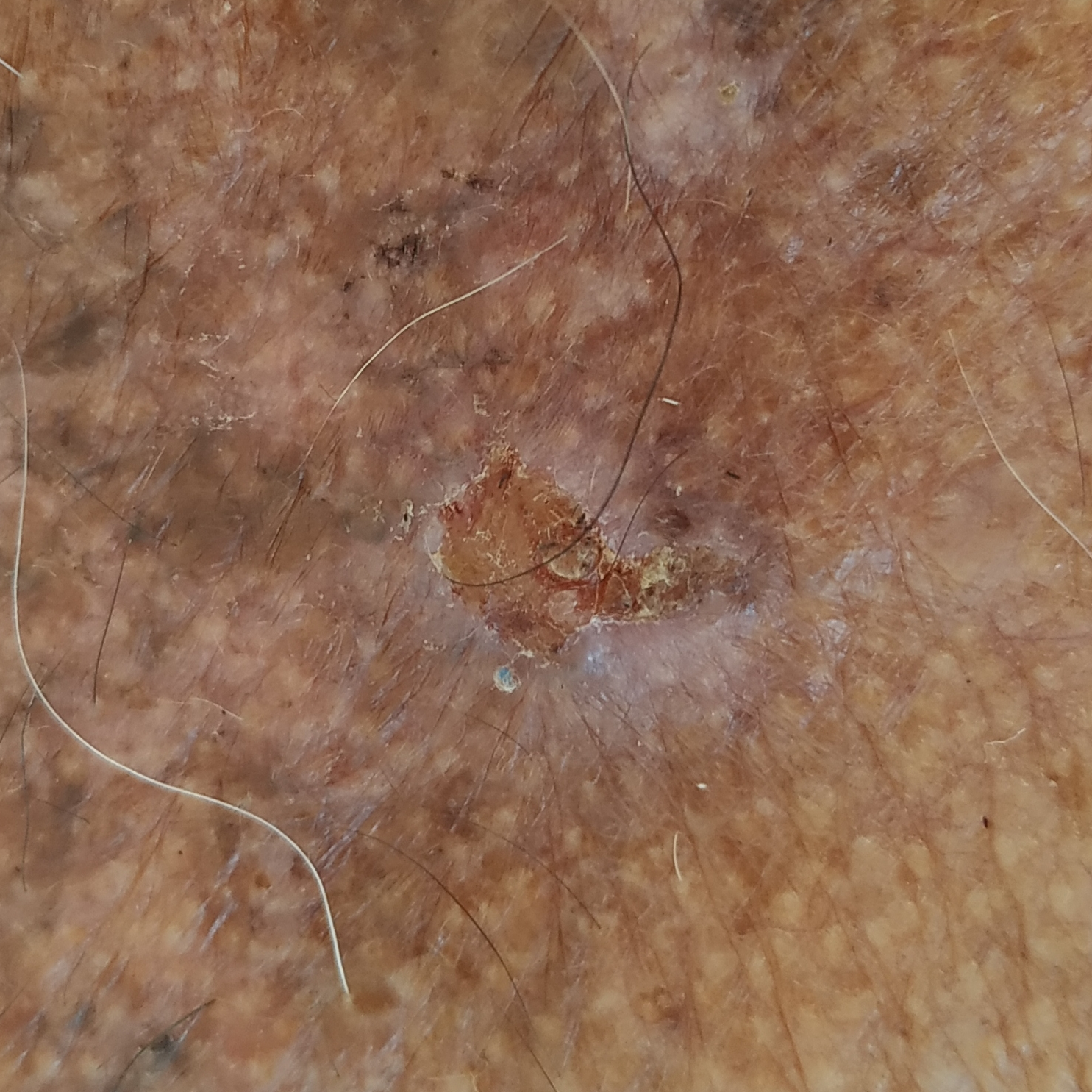The patient was assessed as skin type IV. A clinical close-up photograph of a skin lesion. A female patient in their 80s. History notes tobacco use and pesticide exposure. The lesion involves the chest. Measuring about 15 × 10 mm. The patient describes that the lesion itches, is elevated, has grown, and has bled, but has not changed and does not hurt. On biopsy, the diagnosis was a basal cell carcinoma.